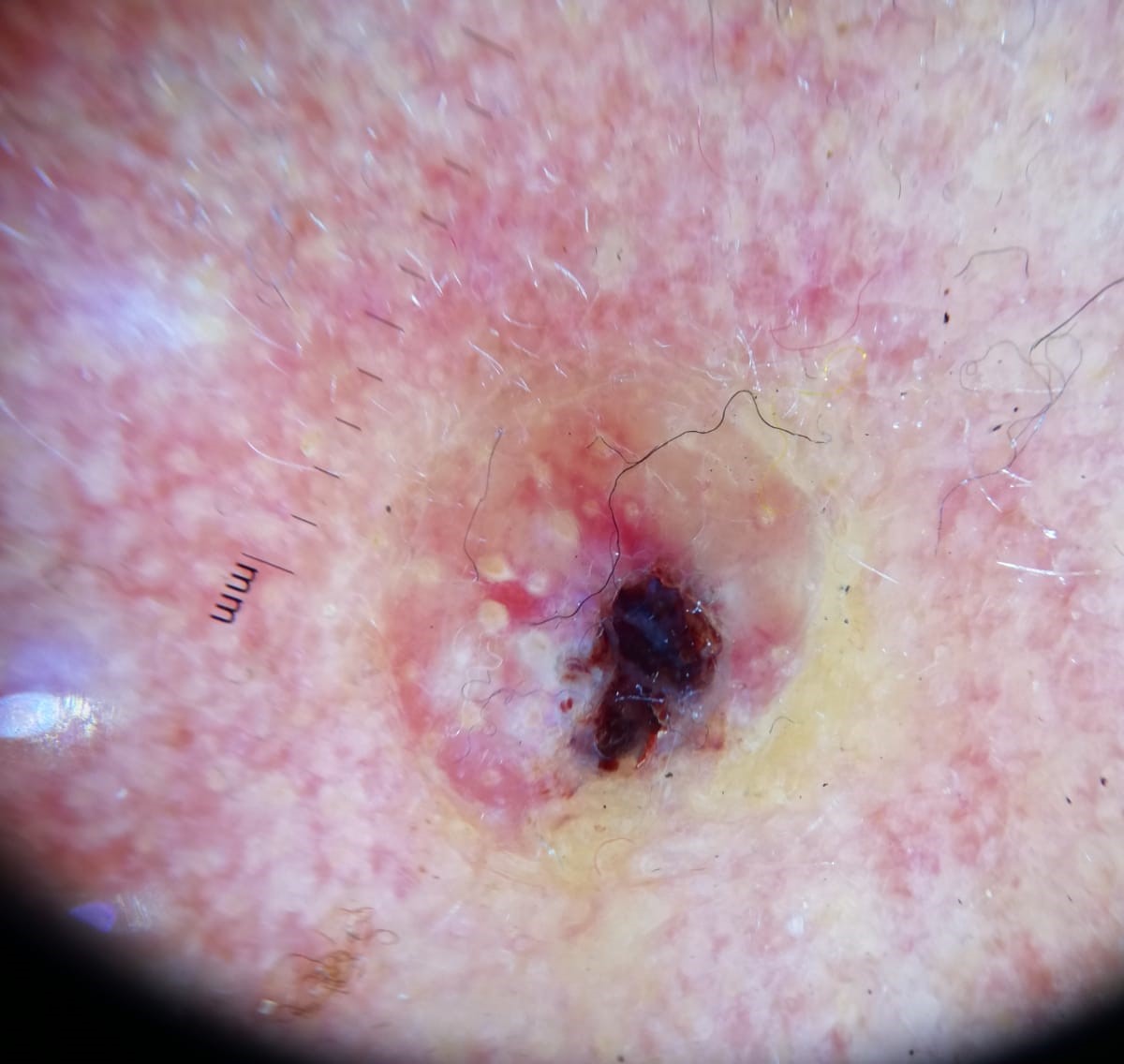Findings: Dermoscopy of a skin lesion. Conclusion: The biopsy diagnosis was a malignant lesion — a squamous cell carcinoma.